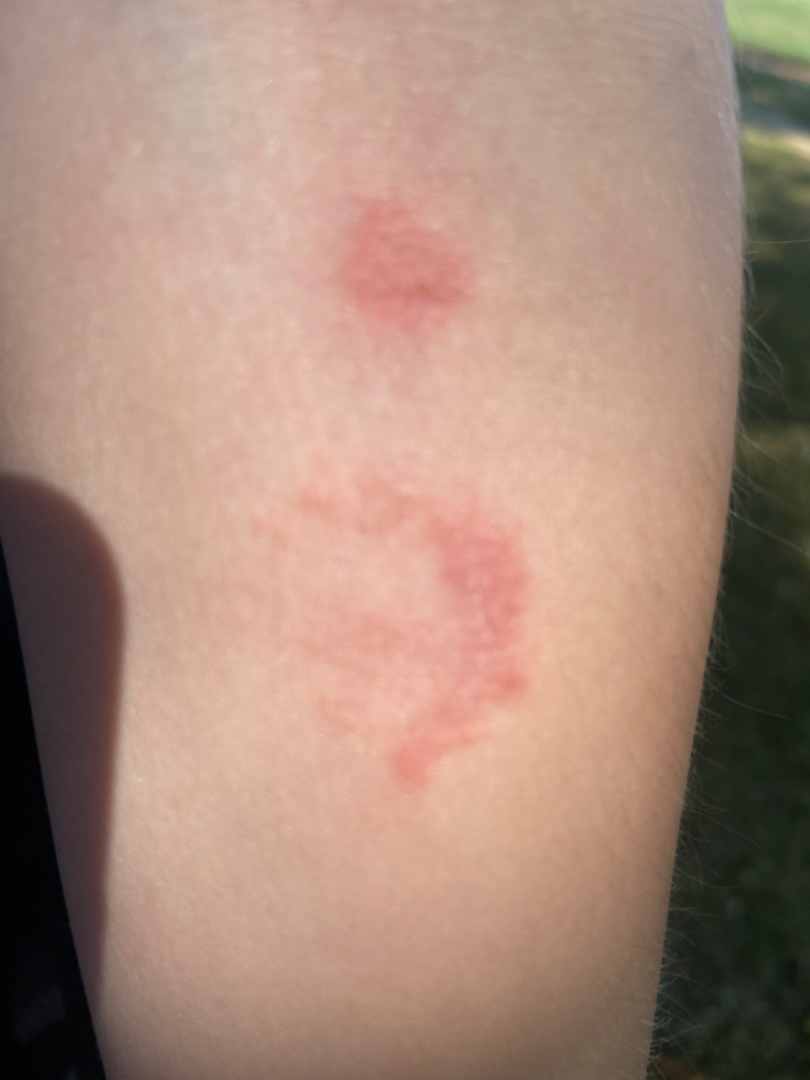No differential diagnosis could be assigned on photographic review. Located on the arm. The patient considered this a rash. Texture is reported as flat. This is a close-up image.